The photograph was taken at a distance; the affected area is the top or side of the foot — 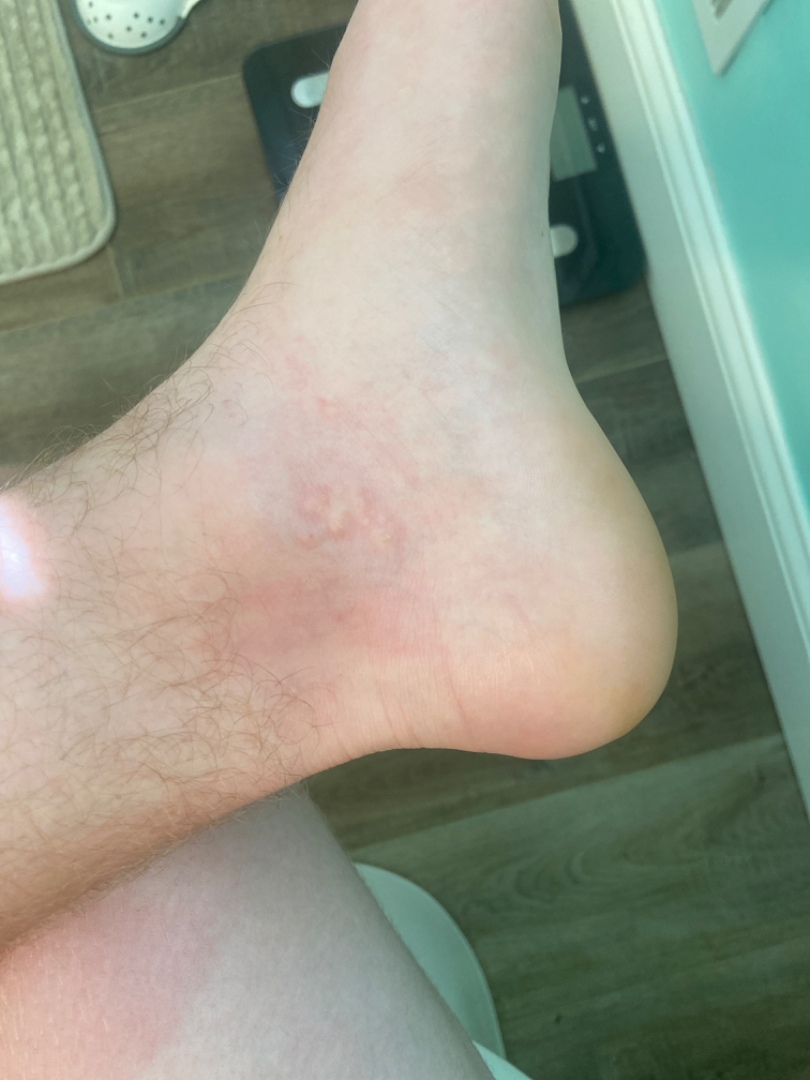Findings: No differential diagnosis could be assigned on photographic review.